A dermoscopic view of a skin lesion, a female patient approximately 70 years of age — 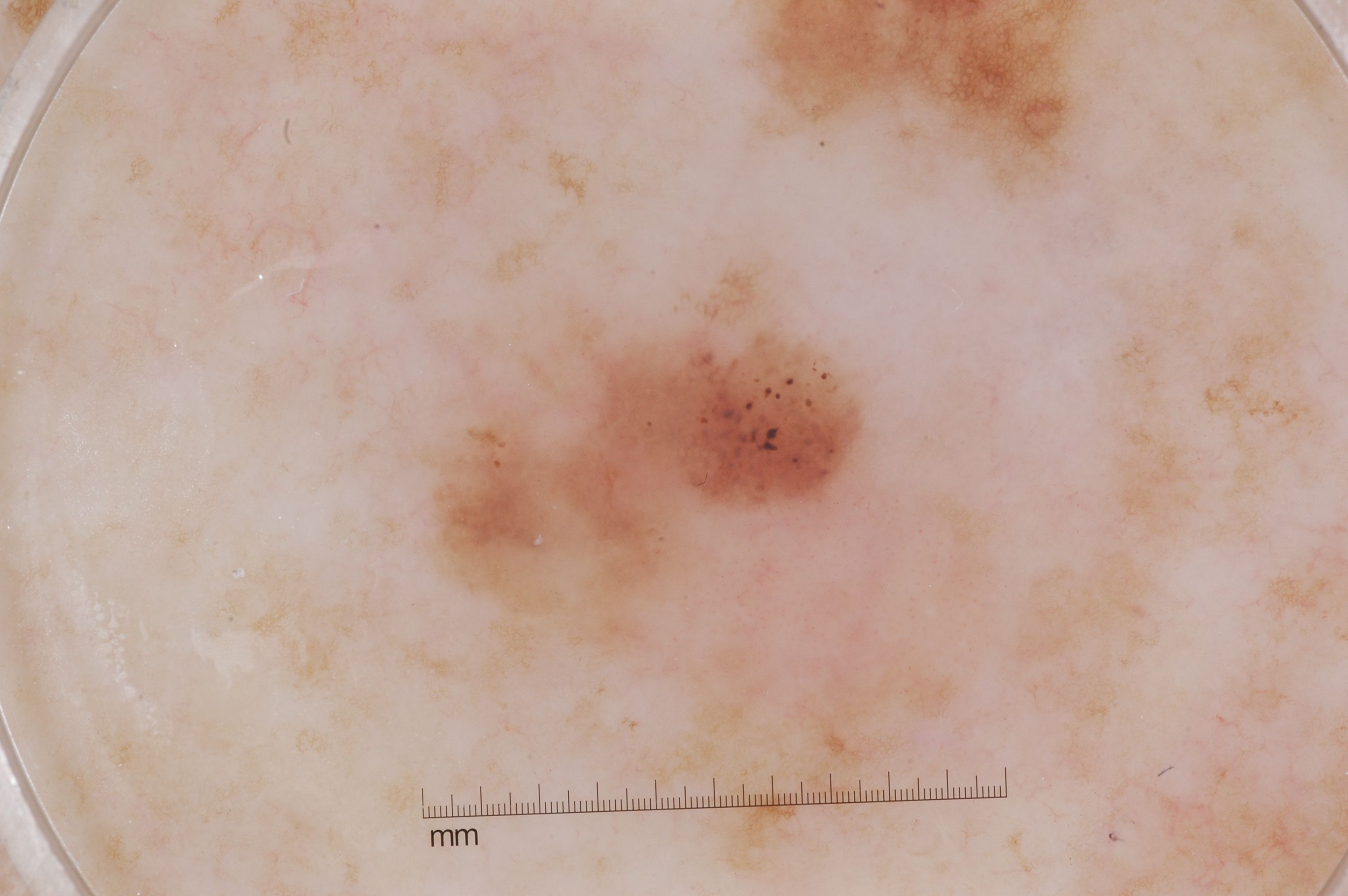dermoscopic findings = pigment network and milia-like cysts; absent: streaks and negative network | extent = ~25% of the field | lesion location = 326/222/1003/850 | diagnostic label = a melanoma.